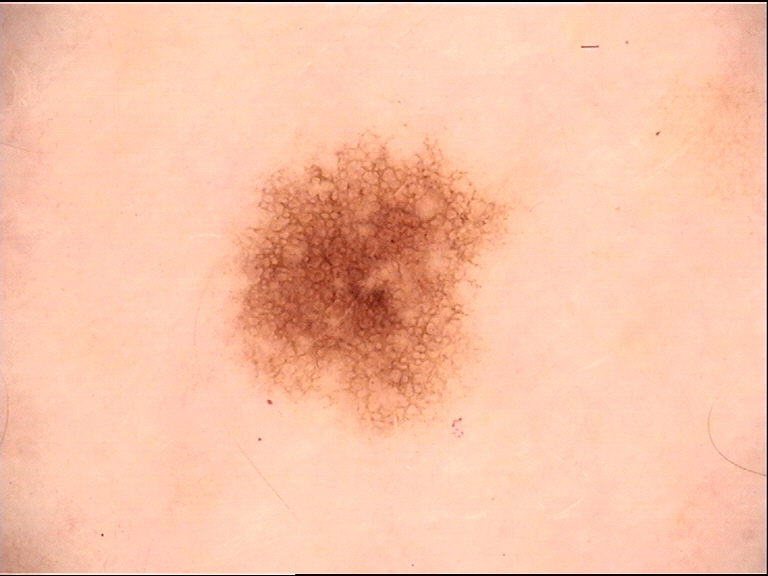A dermoscopy image of a single skin lesion. Classified as a dysplastic junctional nevus.